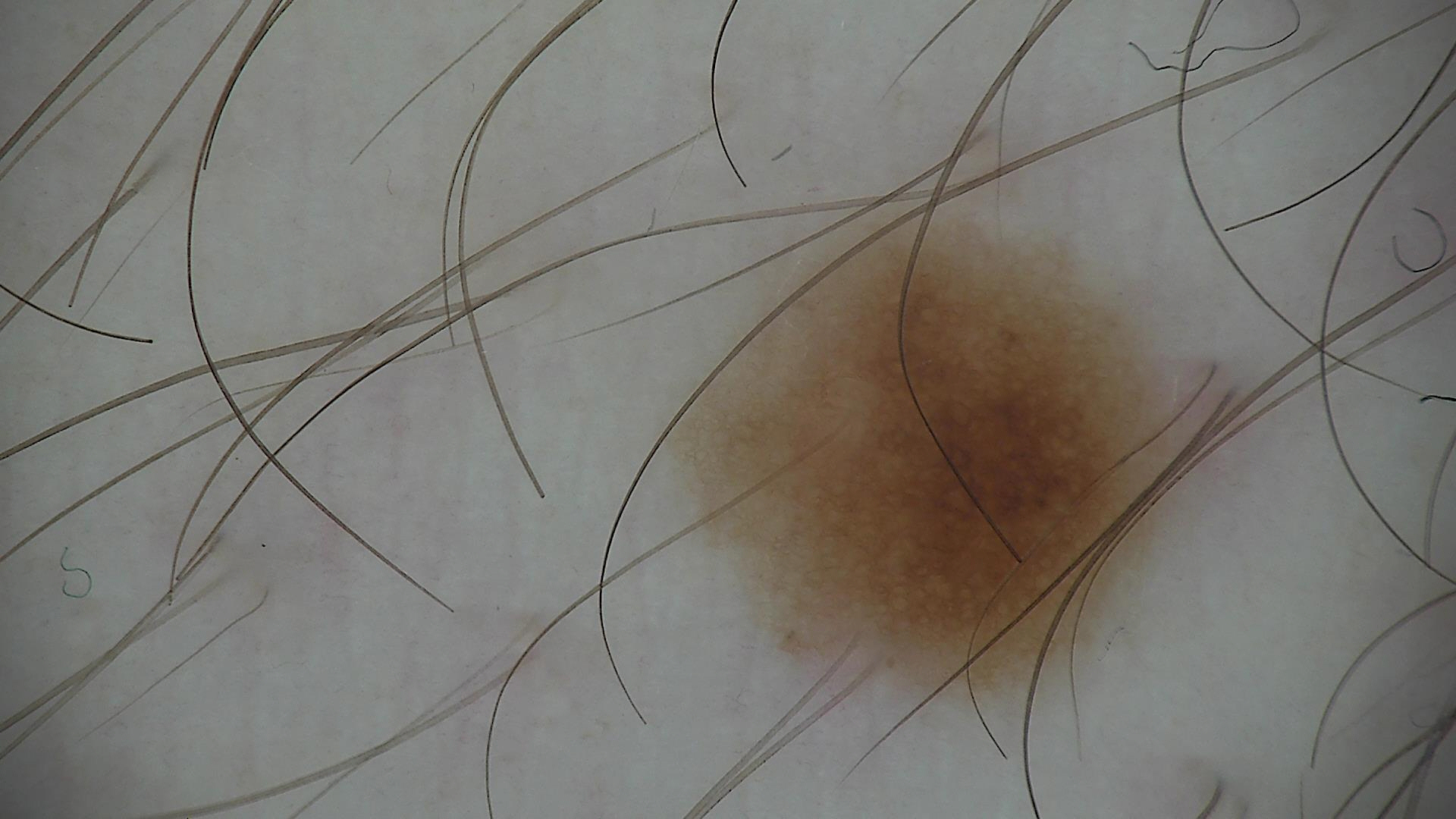- label · dysplastic junctional nevus (expert consensus)